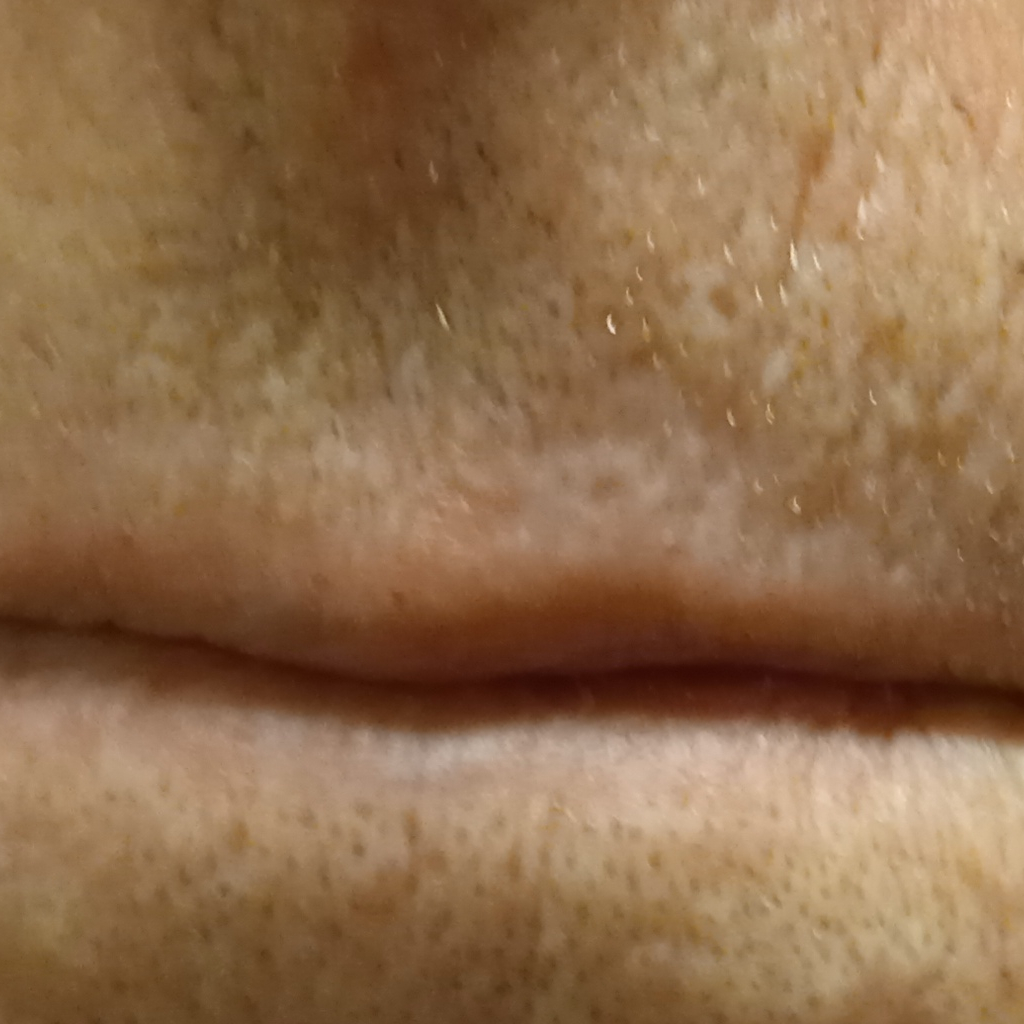nevus count = a moderate number of melanocytic nevi | imaging = clinical photograph | referral context = research study (no referral diagnosis) | patient = male, age 77 | sun reaction = skin reddens with sun exposure | risk factors = a personal history of skin cancer, a personal history of cancer | site = the face | size = 6.4 mm | assessment = actinic keratosis (dermatologist consensus).